A subject in their 60s. A clinical photograph showing a skin lesion — 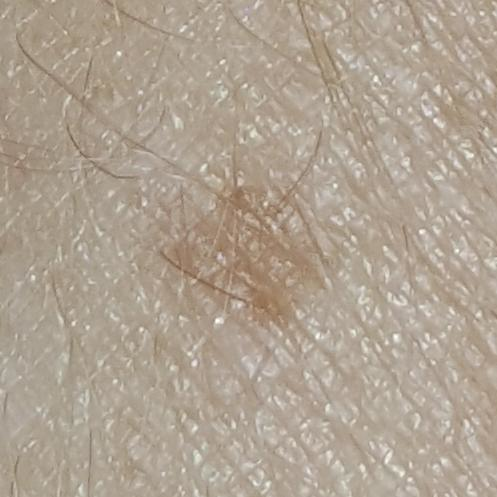symptoms=elevation, growth / no itching
assessment=seborrheic keratosis (clinical consensus)